A dermatoscopic image of a skin lesion · a male patient in their 80s: 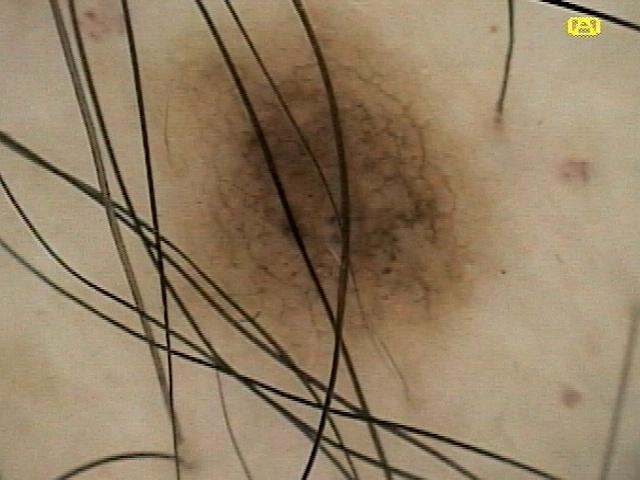Assessment:
Consistent with a melanocytic lesion — a nevus.